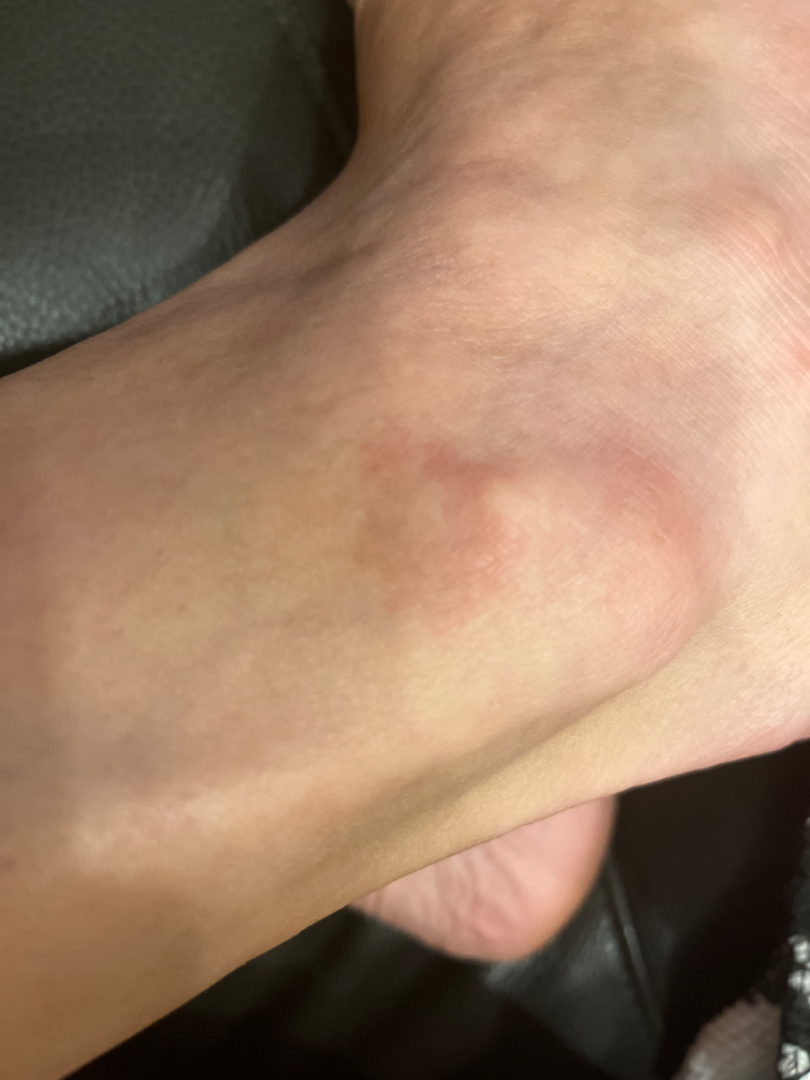diagnostic considerations=Eczema (most likely); Pigmented purpuric eruption (possible)